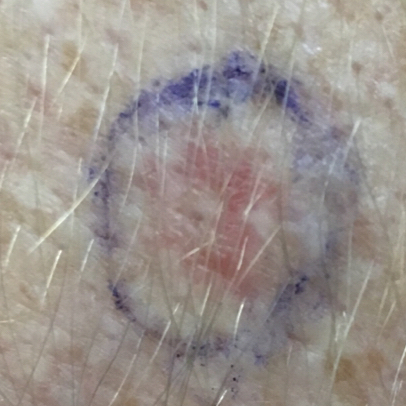A male subject 53 years of age. The patient was assessed as FST I. A clinical close-up photograph of a skin lesion. Located on the face. The lesion measures 4 × 3 mm. By the patient's account, the lesion is elevated, has bled, has grown, hurts, and itches. Confirmed on histopathology as a basal cell carcinoma.